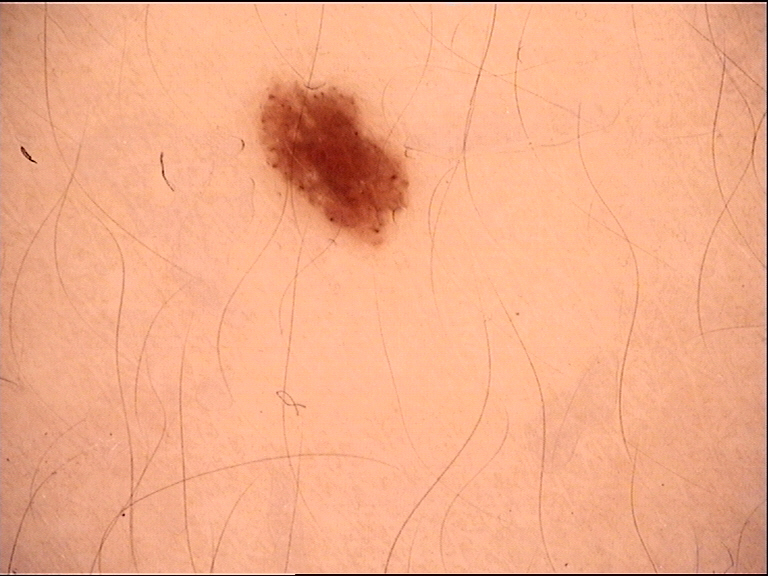Impression:
Diagnosed as a dysplastic junctional nevus.